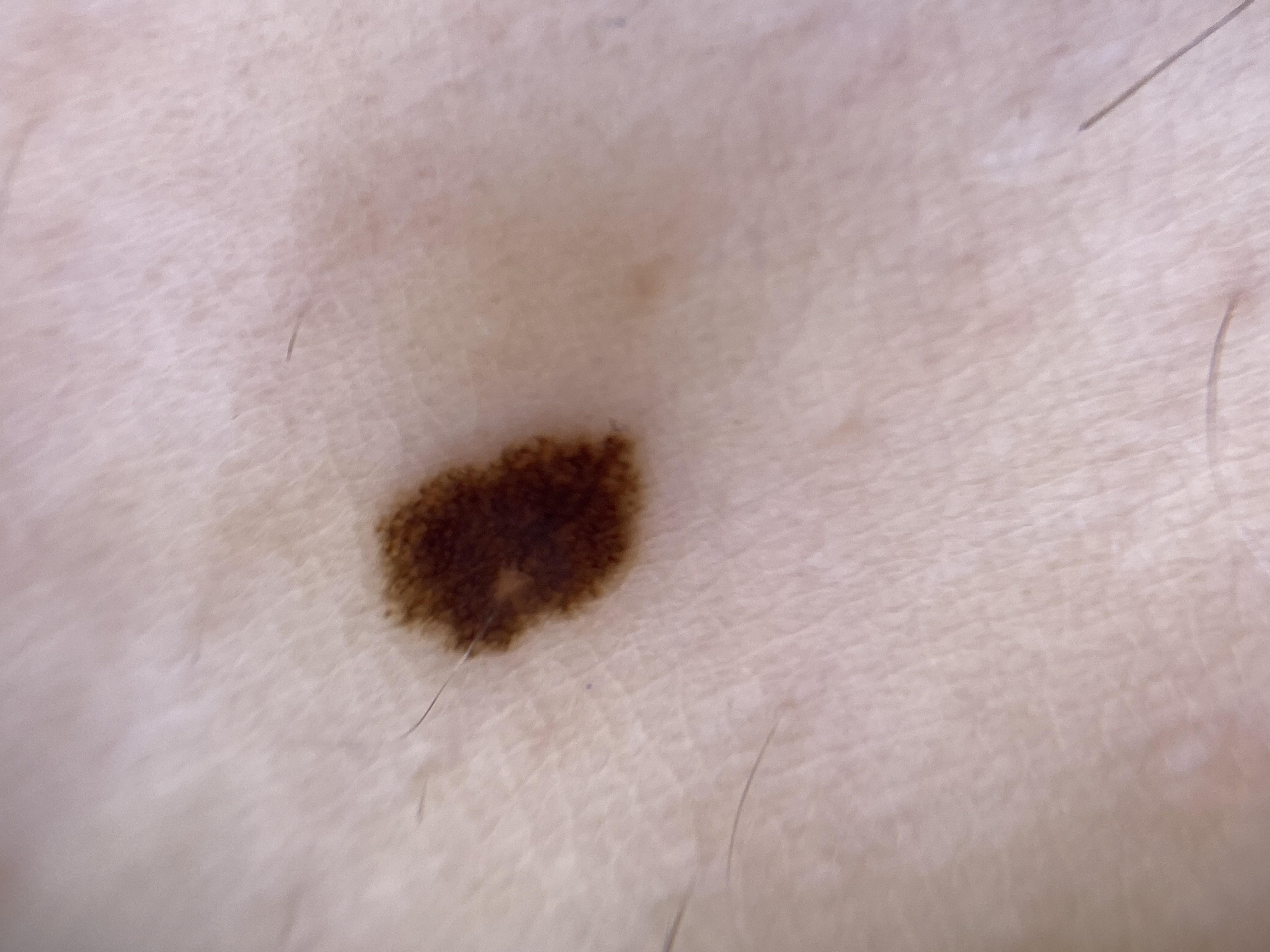Case:
• patient — female, roughly 20 years of age
• image — dermoscopy
• location — a lower extremity
• diagnostic label — Nevus (clinical impression)